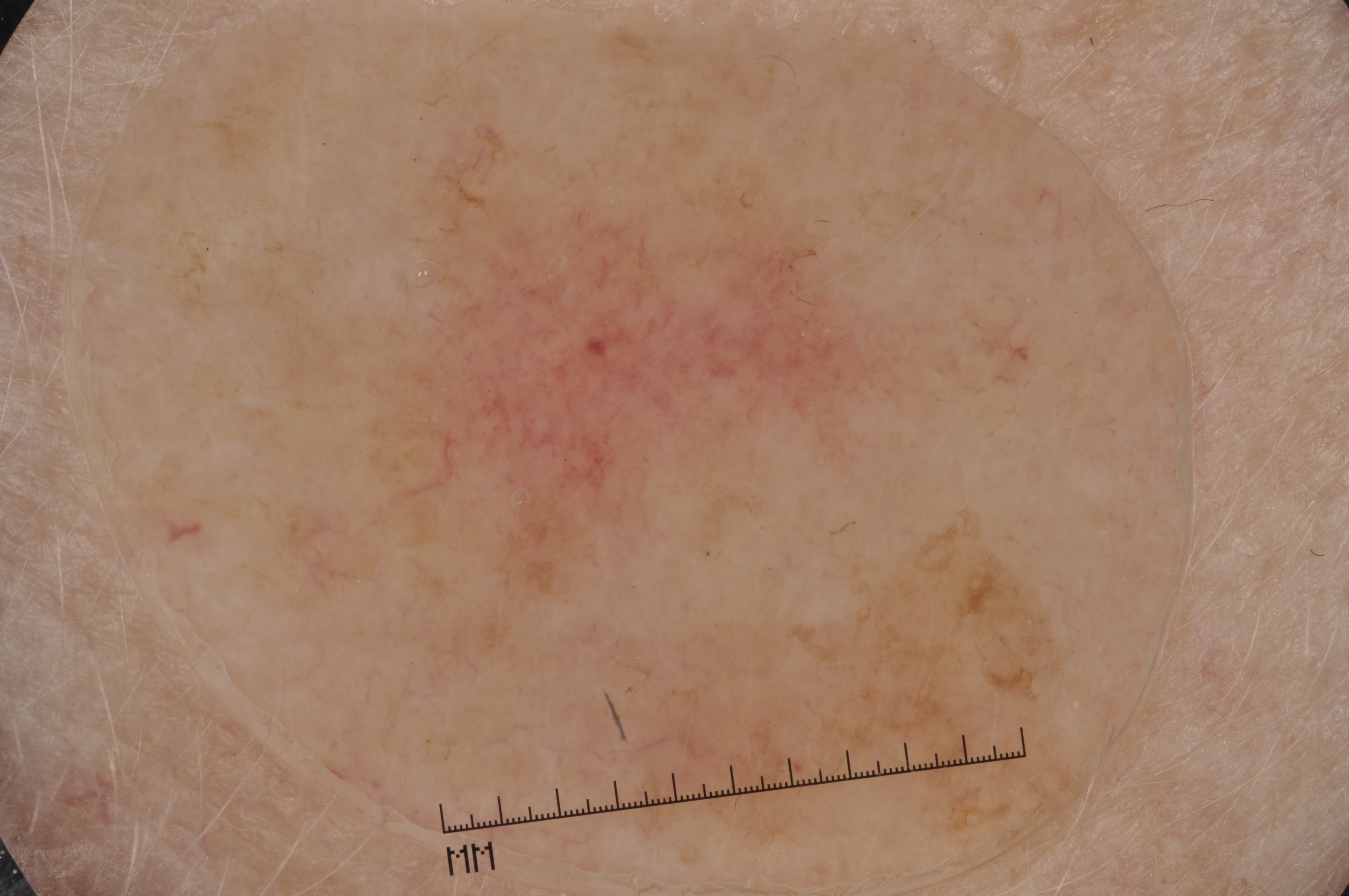Q: What is the imaging modality?
A: dermoscopy
Q: What are the patient's age and sex?
A: female, aged around 55
Q: Which assessed dermoscopic features were absent?
A: milia-like cysts, pigment network, negative network, and streaks
Q: What is the lesion's bounding box?
A: <bbox>146, 15, 1115, 877</bbox>
Q: How much of the field does the lesion occupy?
A: ~57% of the field
Q: What is this lesion?
A: a seborrheic keratosis, a benign lesion